The subject is a male about 30 years old. A dermoscopic close-up of a skin lesion: 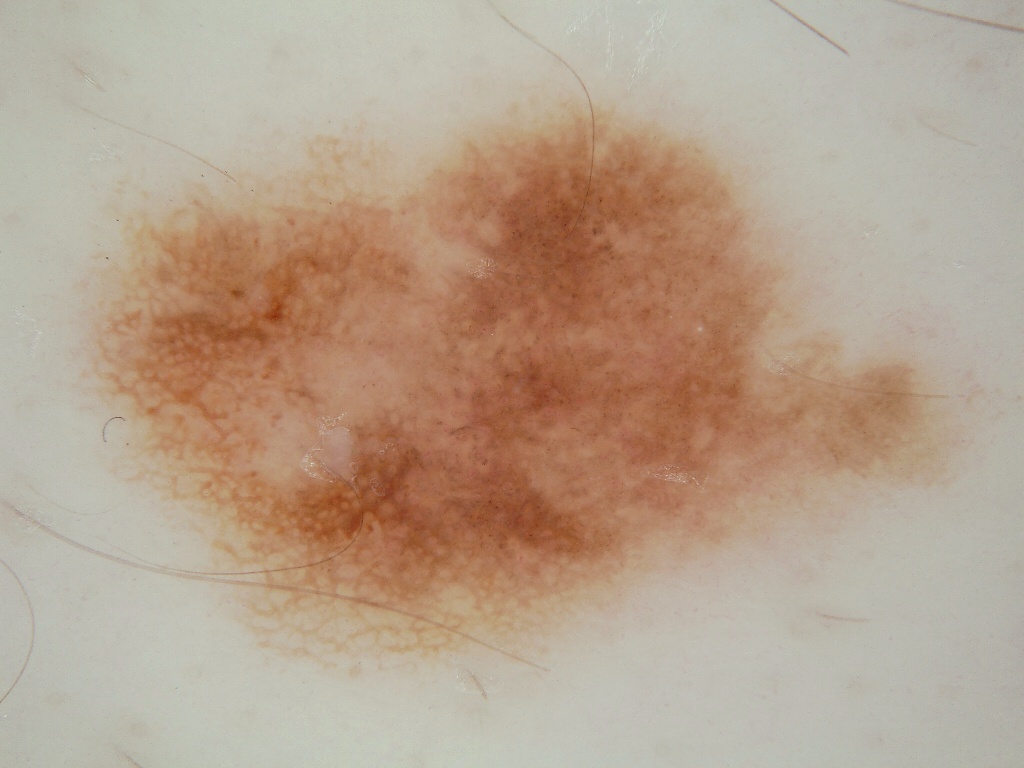Notes:
• dermoscopic findings — milia-like cysts and pigment network
• bounding box — bbox=[78, 94, 977, 663]
• size — large
• assessment — a melanocytic nevus